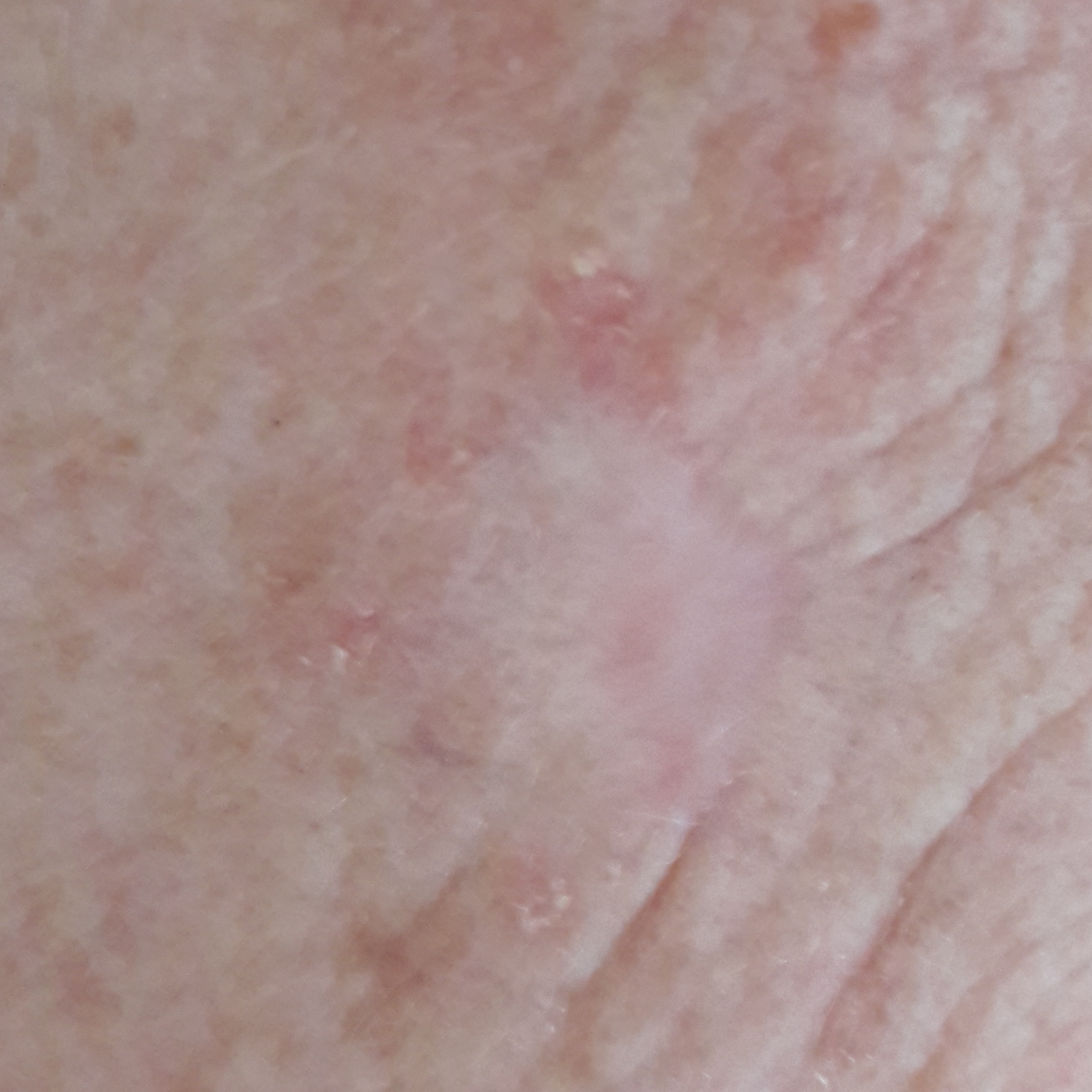Patient and lesion:
A female subject 56 years old. A clinical photograph of a skin lesion. The lesion is on the face. Measuring about 13 × 12 mm.
Pathology:
The biopsy diagnosis was an actinic keratosis.